A dermoscopic view of a skin lesion, the subject is a male aged 48 to 52: 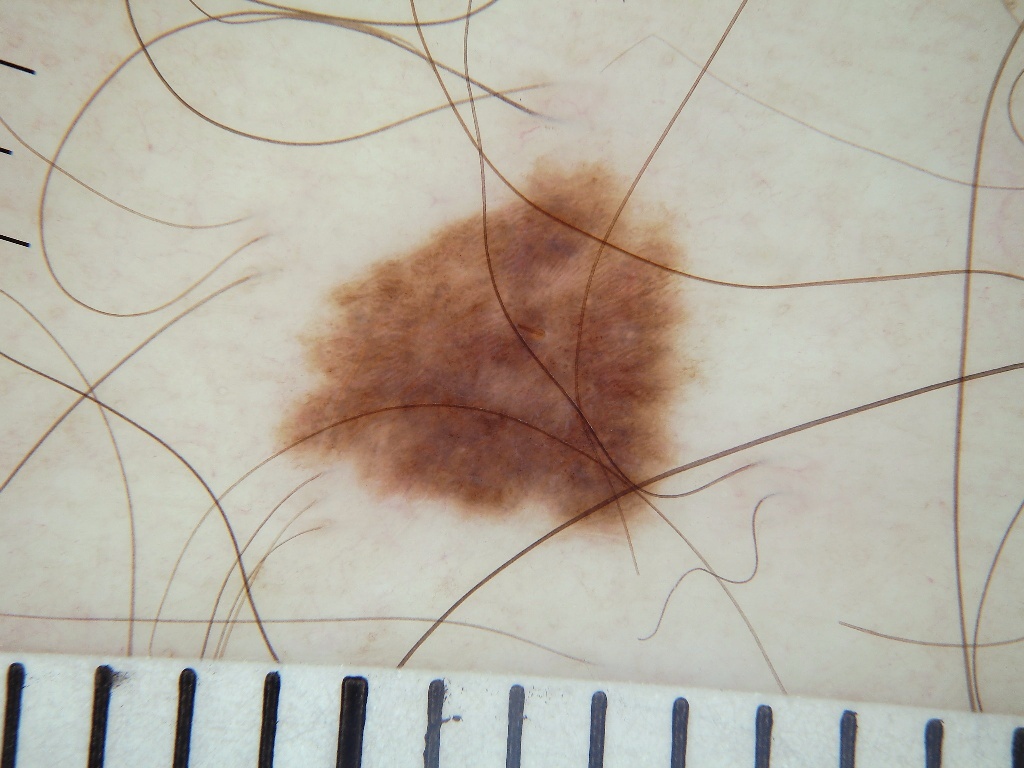Dermoscopically, the lesion shows negative network and globules. With coordinates (x1, y1, x2, y2), the lesion is located at 270 149 715 540. The lesion covers approximately 16% of the dermoscopic field. The diagnostic assessment was a melanocytic nevus.